A skin lesion imaged with a dermatoscope:
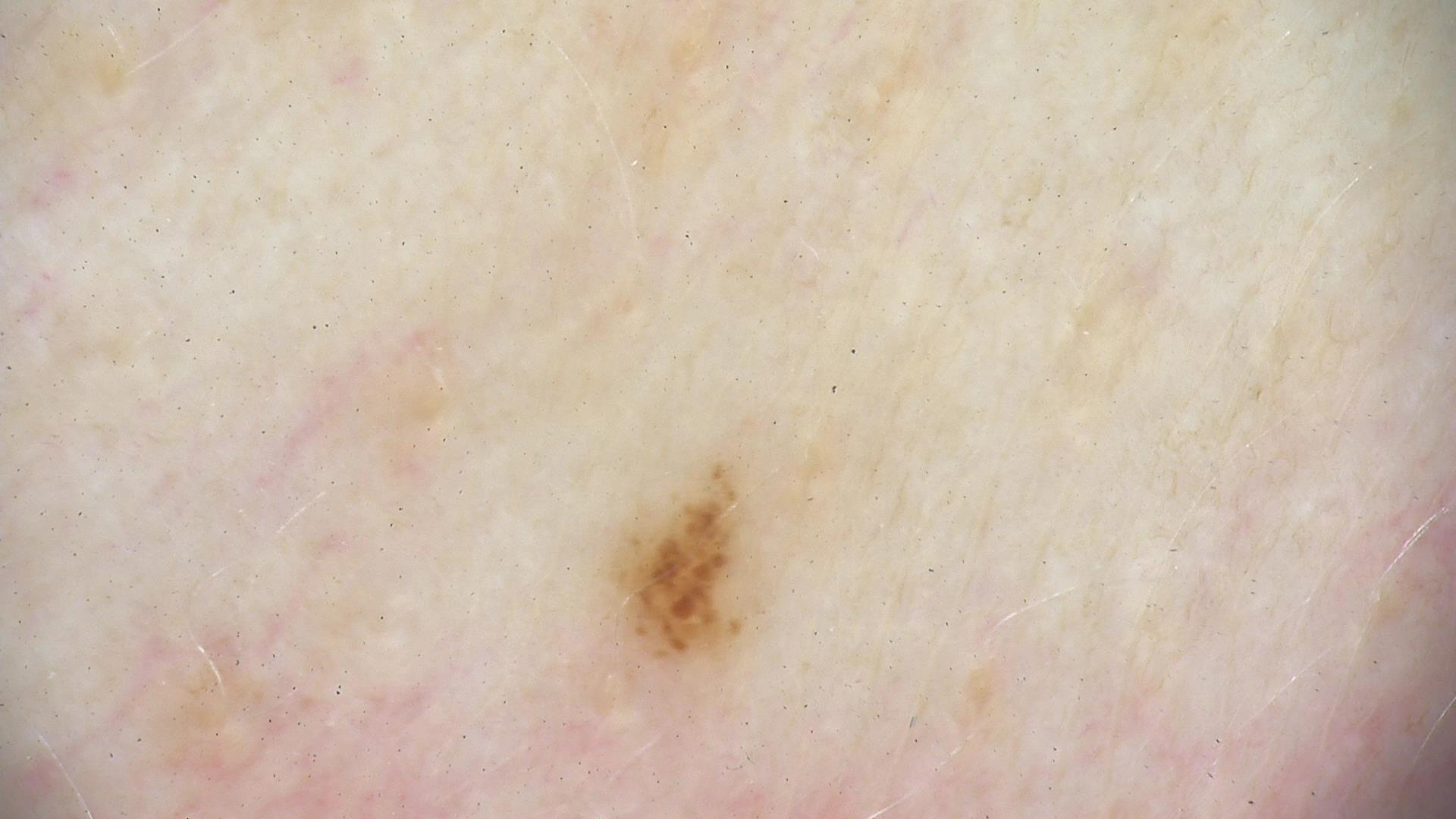– diagnosis · dysplastic junctional nevus (expert consensus)